A dermoscopy image of a single skin lesion: 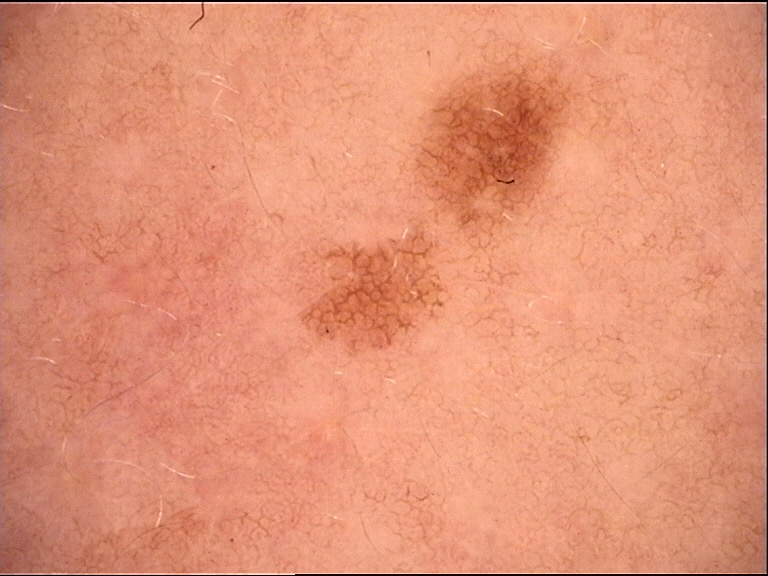Classified as a solar lentigo.